The lesion is associated with burning, itching, bothersome appearance, enlargement, pain, darkening and bleeding; located on the arm; the patient indicates the condition has been present for one to four weeks; the lesion is described as fluid-filled; the patient indicates associated fatigue, fever and joint pain; the patient is 50–59, female; the photo was captured at an angle — 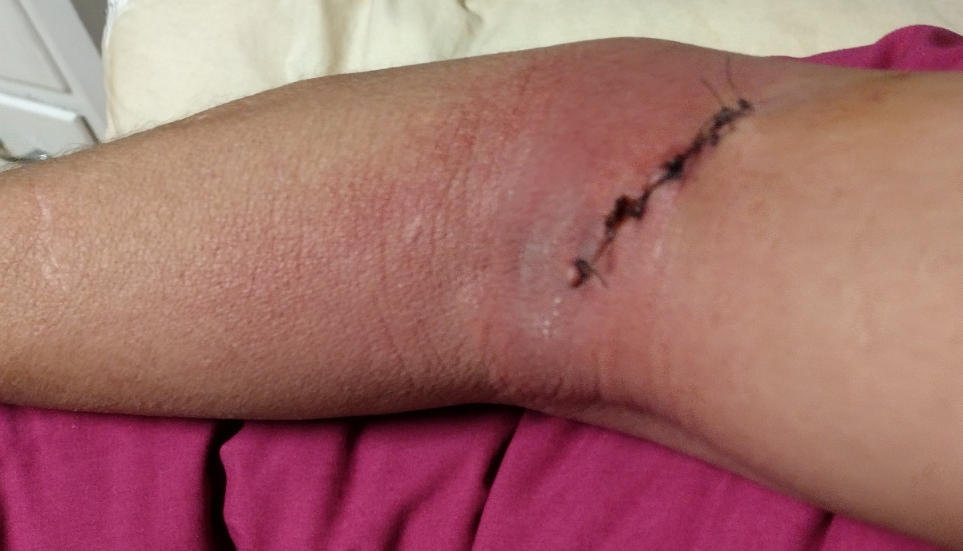Q: What conditions are considered?
A: most likely Inflicted skin lesions; also raised was Skin ulcer; also consider Dehiscence